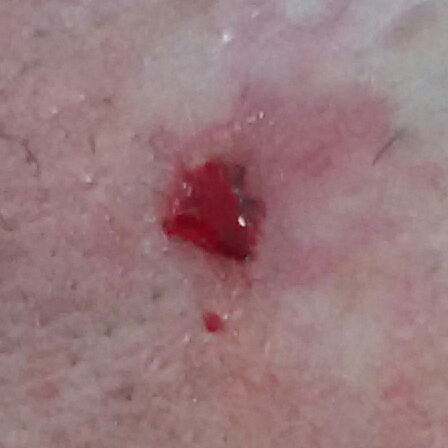The chart notes prior skin cancer (patient or family), prior malignancy (patient or family), pesticide exposure, and no tobacco use. Fitzpatrick skin type III. A clinical photo of a skin lesion taken with a smartphone. A male subject 62 years of age. Located on the face. The lesion is roughly 9 by 6 mm. The patient reports that the lesion has bled, itches, hurts, has grown, and has changed, but is not elevated. Histopathological examination showed a basal cell carcinoma.